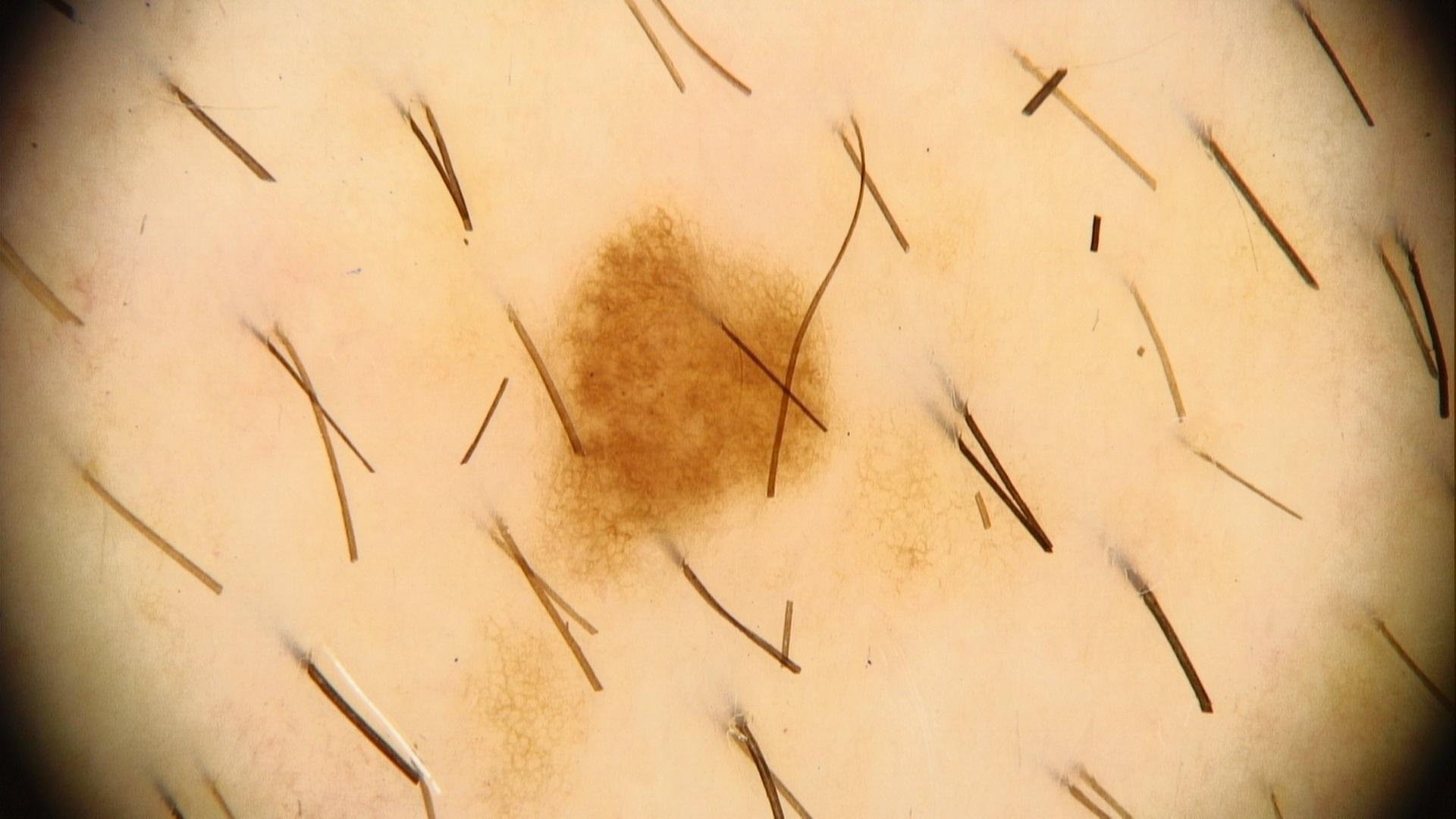A male subject in their 60s. The lesion is located on the trunk. Clinically diagnosed as a benign lesion — a nevus.